A dermoscopic image of a skin lesion.
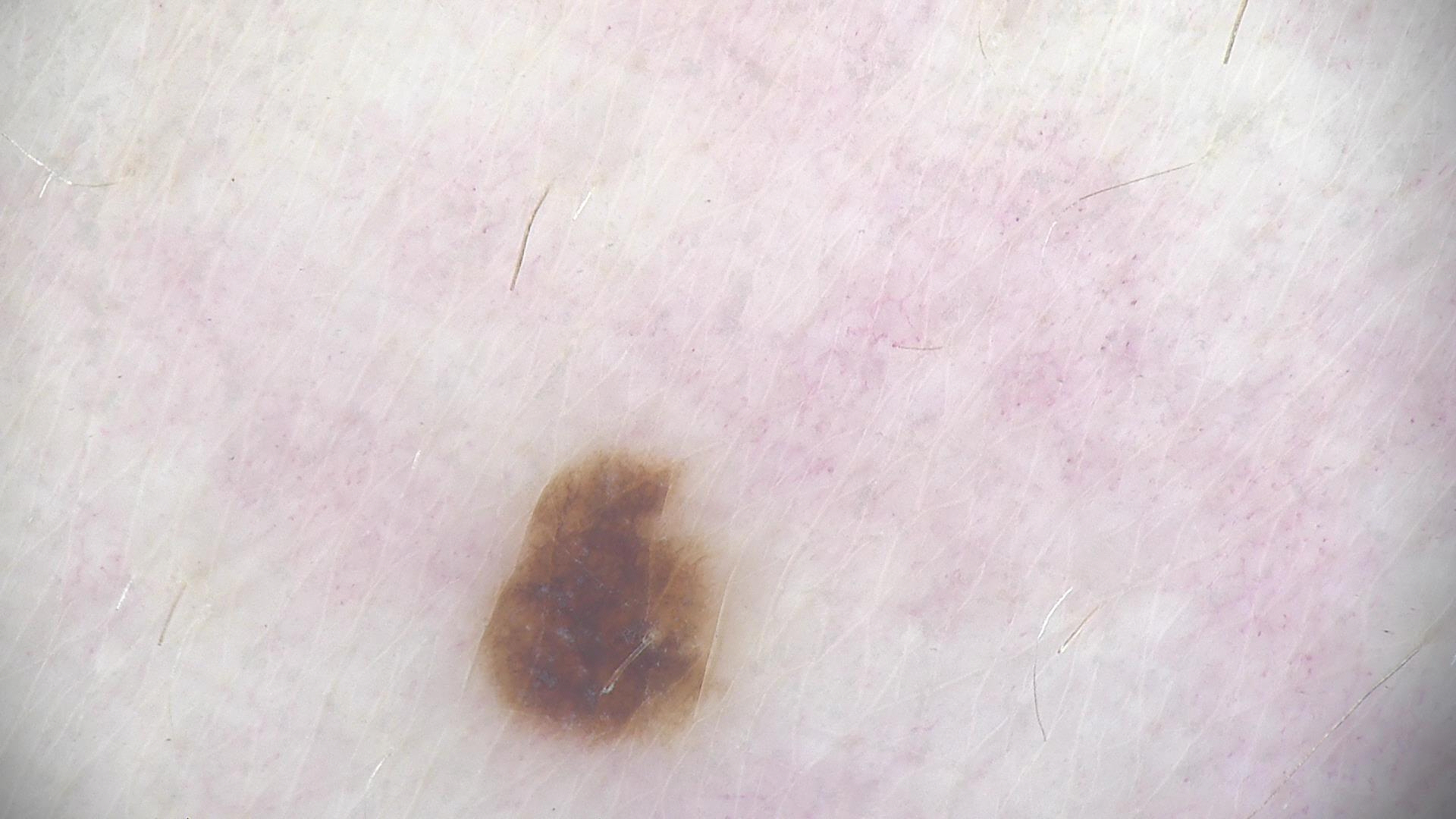Q: What is the diagnosis?
A: dysplastic junctional nevus (expert consensus)